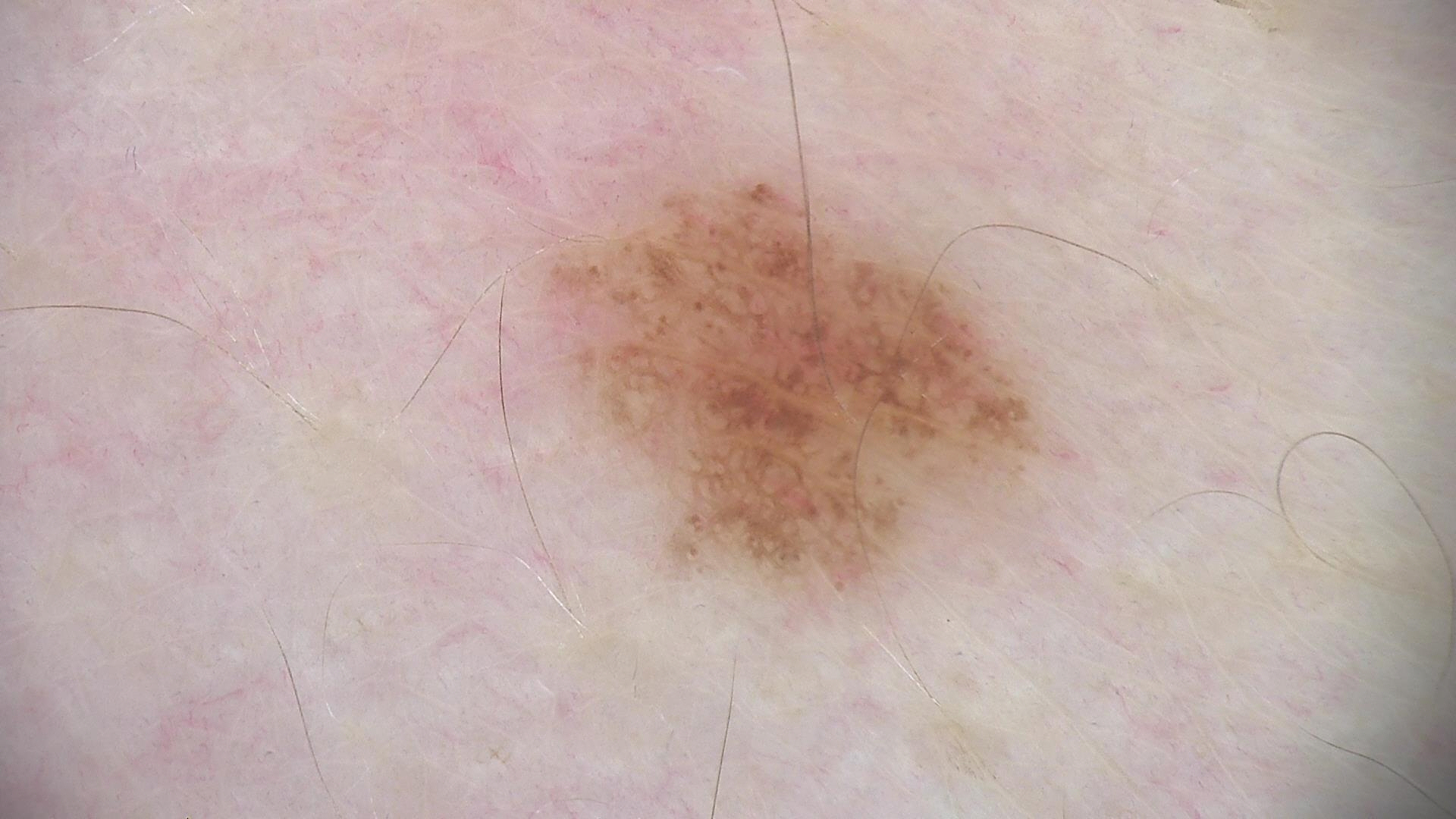• imaging · dermatoscopy
• diagnostic label · dysplastic junctional nevus (expert consensus)